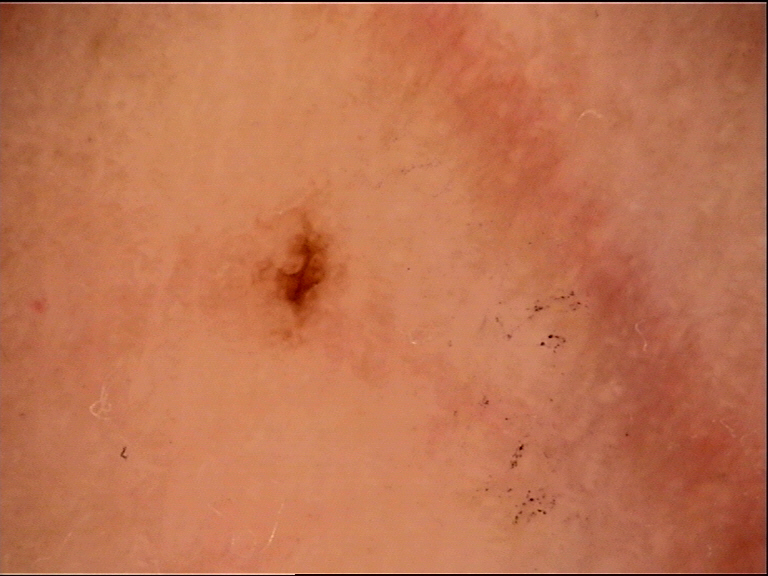image=dermatoscopy
diagnostic label=acral dysplastic junctional nevus (expert consensus)